A skin lesion imaged with a dermatoscope; a female patient aged around 45:
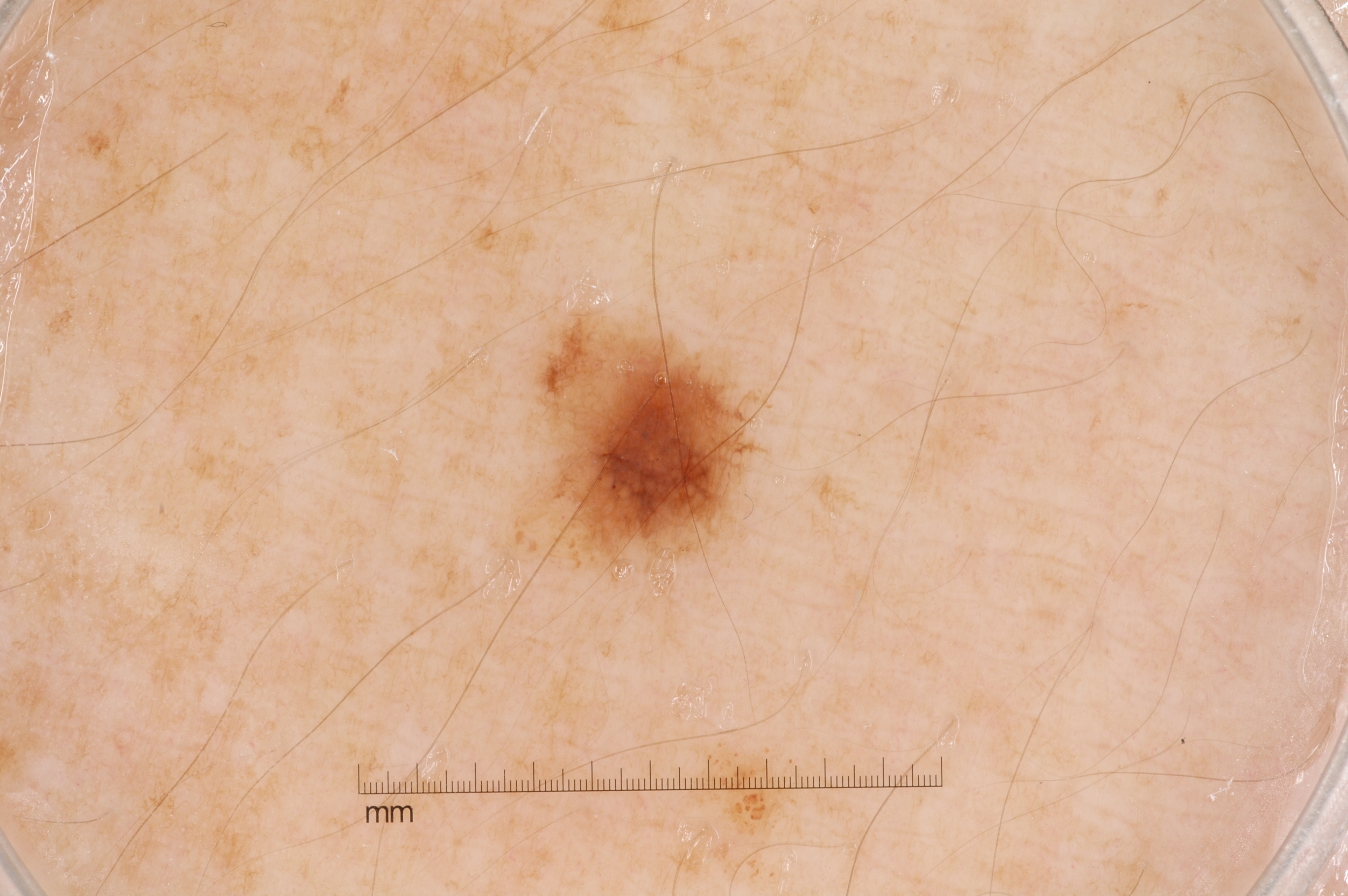Findings:
– extent — small
– dermoscopic pattern — pigment network; absent: milia-like cysts, negative network, and streaks
– location — left=537, top=329, right=747, bottom=560
– diagnosis — a melanocytic nevus, a benign skin lesion